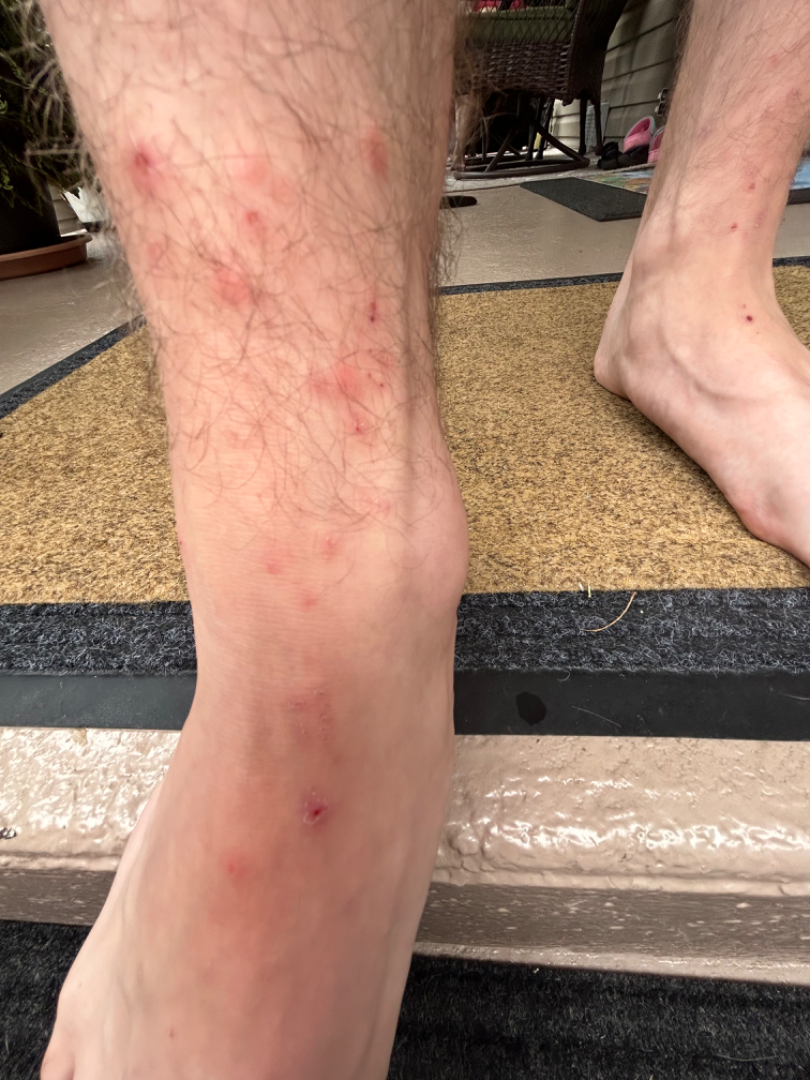Case summary:
* site · leg, arm, top or side of the foot and back of the torso
* subject · male, age 18–29
* image framing · at an angle
* differential · single-reviewer assessment: Insect Bite and Acute dermatitis, NOS were each considered, in no particular order